The lesion is described as raised or bumpy, the condition has been present for about one day, this image was taken at an angle, the back of the hand is involved: 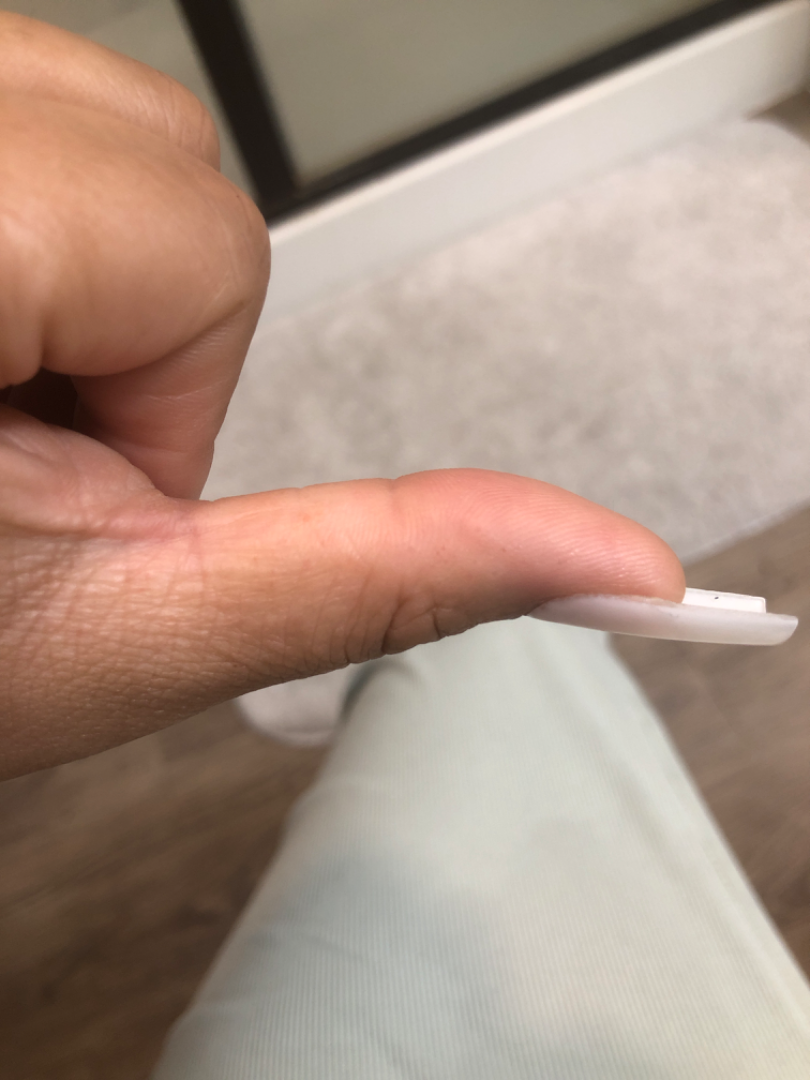assessment: unable to determine